Dermoscopy of a skin lesion — 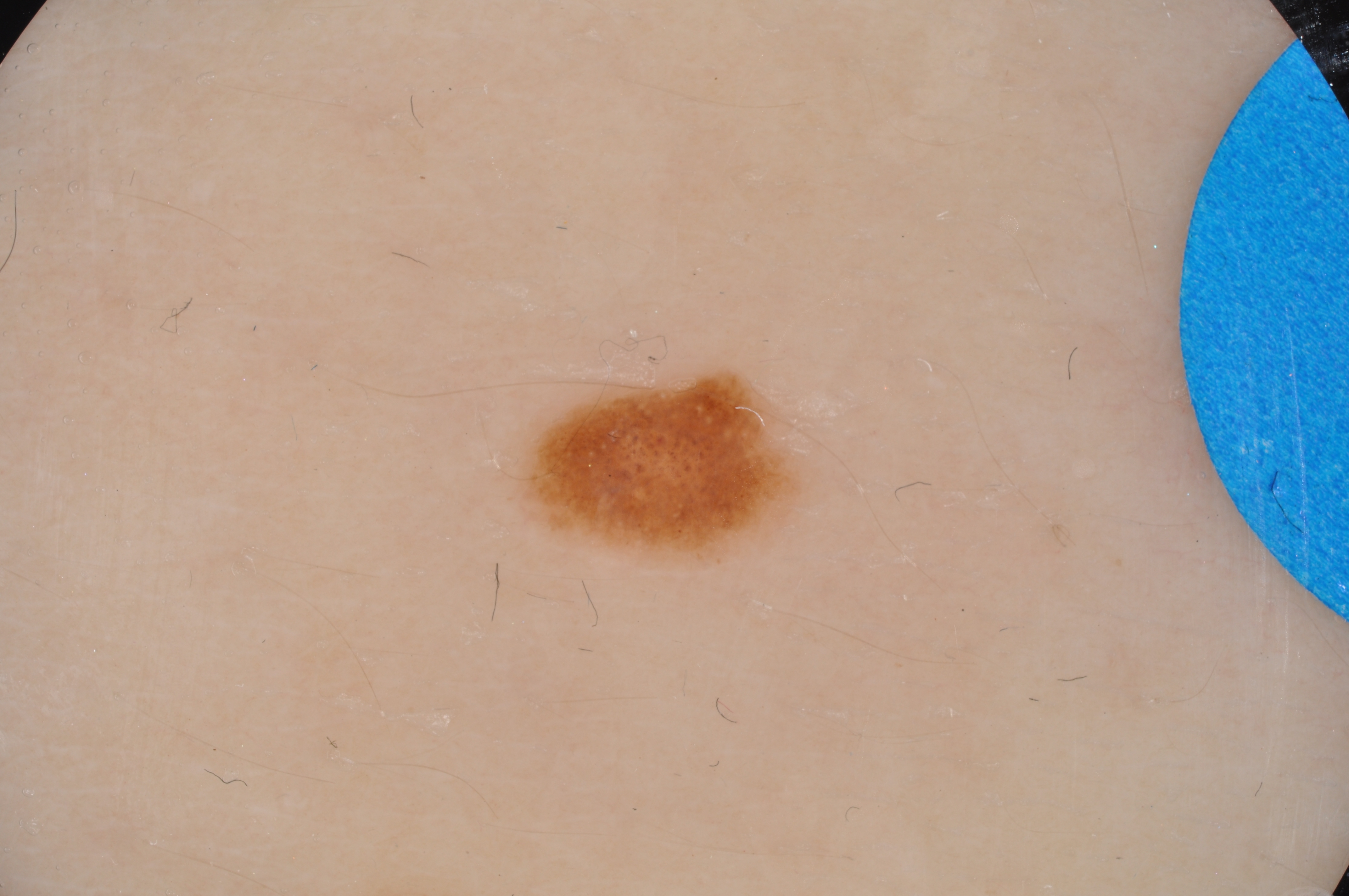* lesion location · 520 370 799 559
* features · globules
* assessment · a melanocytic nevus